The subject is 50–59, female · located on the front of the torso · the photo was captured at an angle — 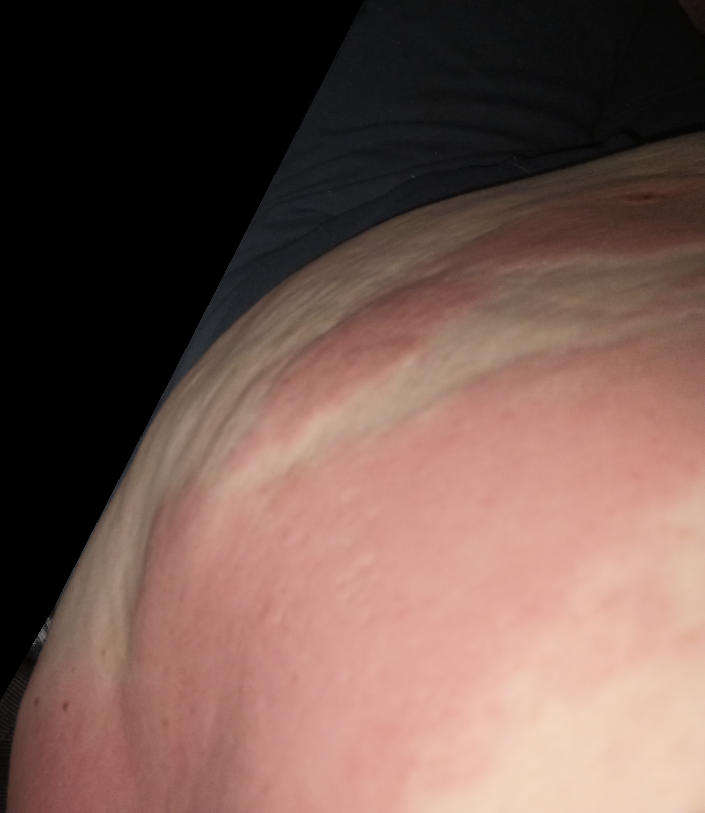Findings:
On remote dermatologist review: the differential includes Contact dermatitis and Urticaria, with no clear leading consideration.